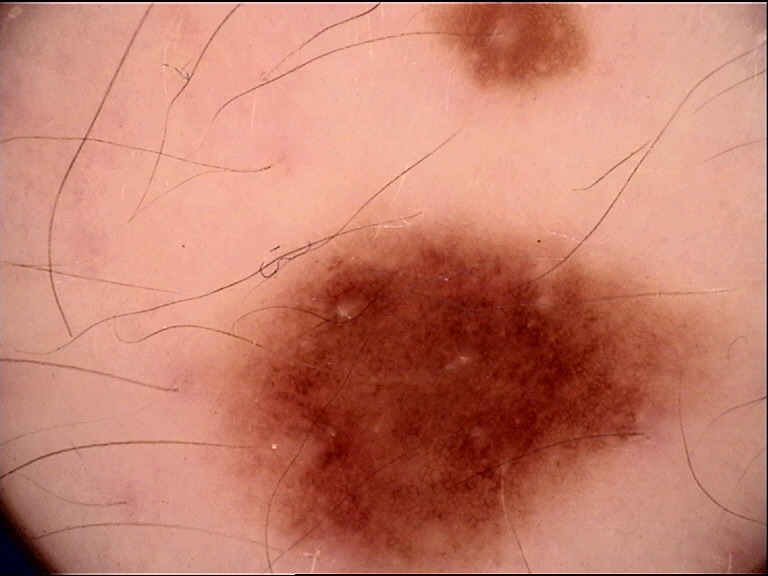diagnosis: dysplastic junctional nevus (expert consensus)